This image was taken at an angle. The lesion involves the arm. Female patient, age 18–29 — 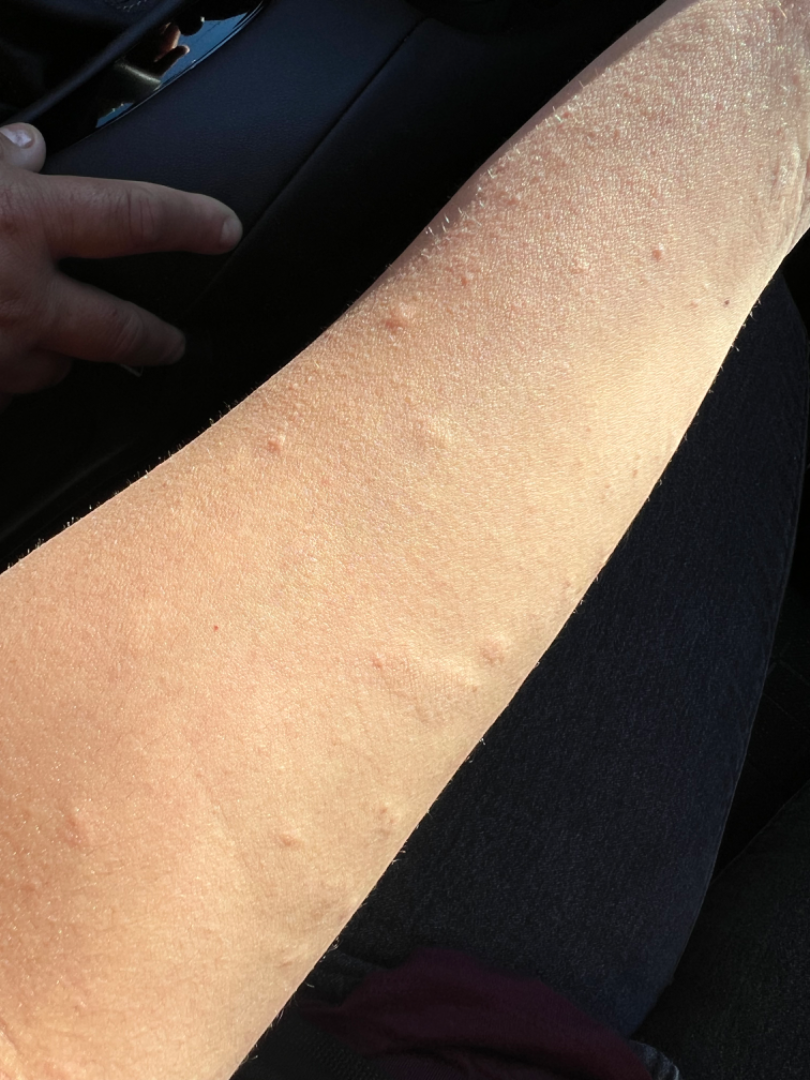Findings: The leading impression is Urticaria; possibly Acute and chronic dermatitis.